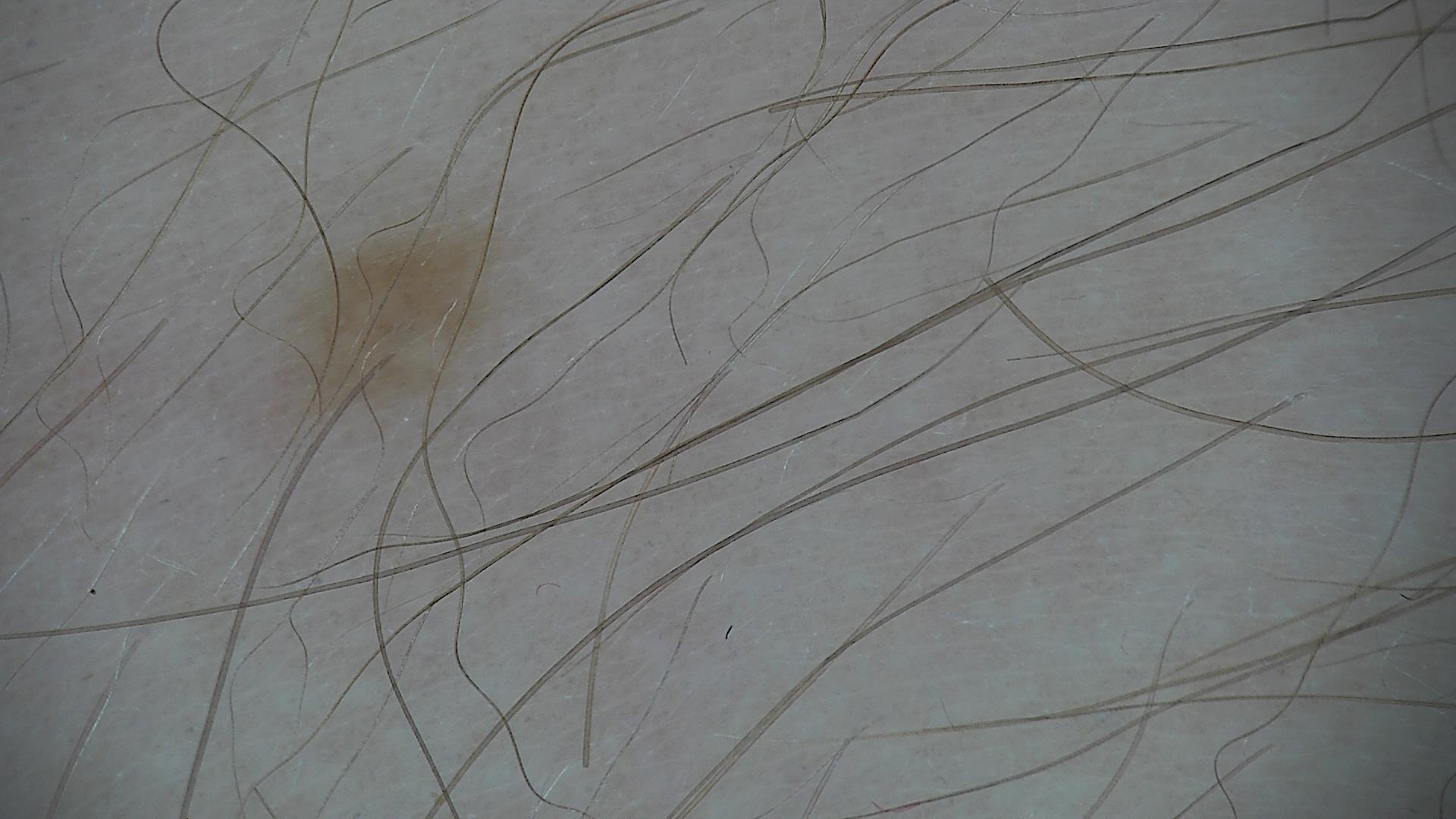A dermatoscopic image of a skin lesion. Classified as a banal lesion — a junctional nevus.